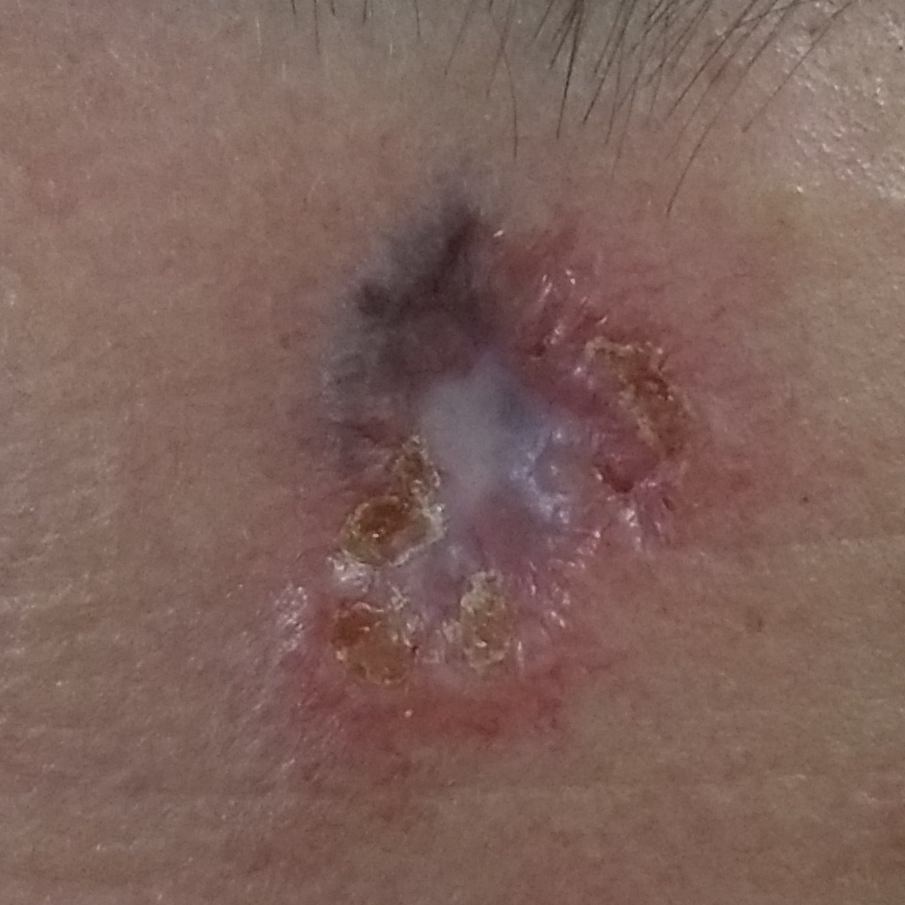Patient and lesion: A female patient in their late 30s. A smartphone photograph of a skin lesion. Located on the face. Diagnosis: Histopathological examination showed a basal cell carcinoma.